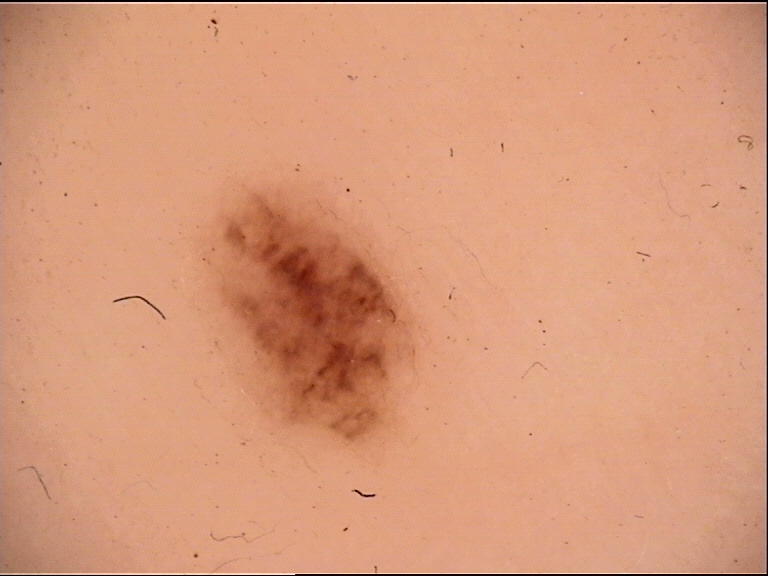Diagnosed as an acral compound nevus.